A dermoscopic photograph of a skin lesion.
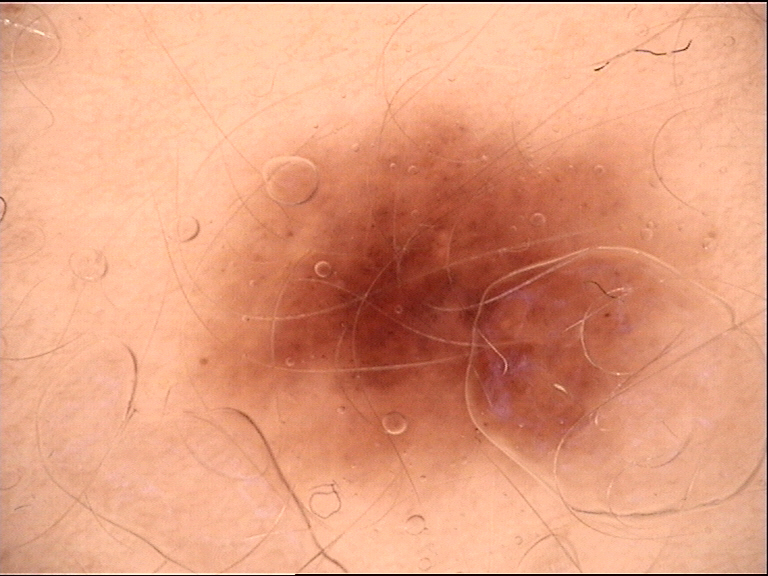diagnostic label: dysplastic junctional nevus (expert consensus)